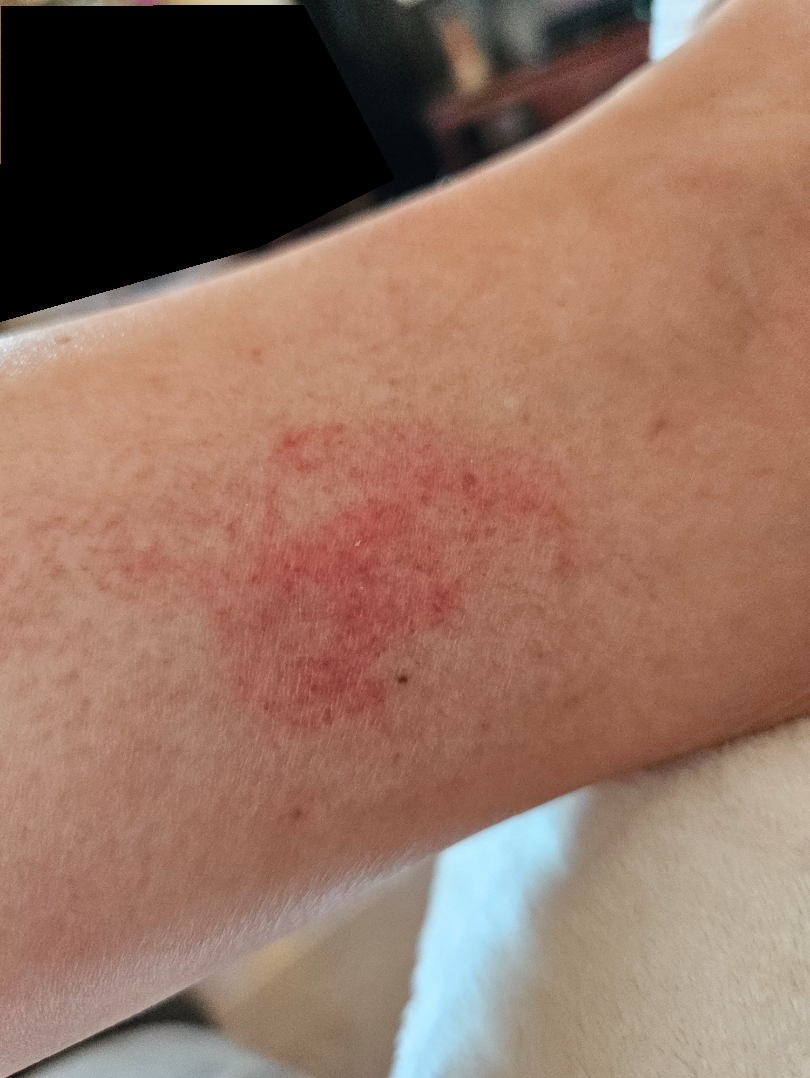The case was difficult to assess from the available photograph. The leg is involved. A close-up photograph. No constitutional symptoms were reported.